The contributor is 40–49, female · a close-up photograph · the leg is involved — 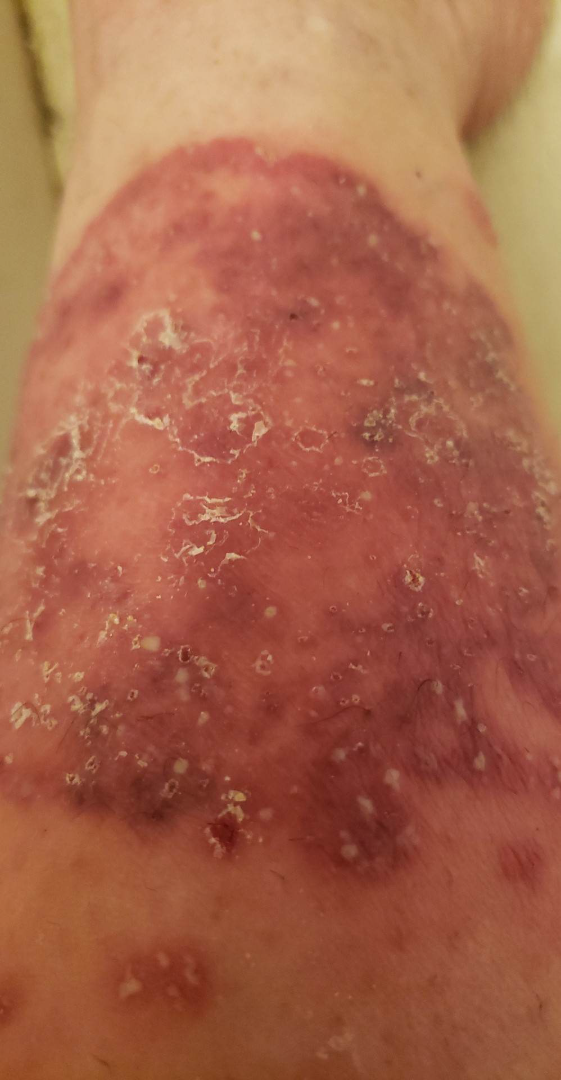On photographic review, the differential, in no particular order, includes Psoriasis, Deep fungal infection and Eczema.